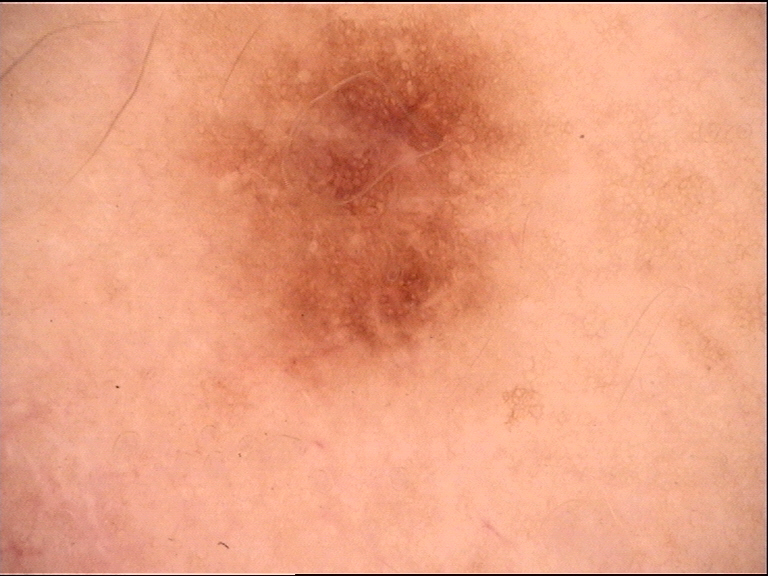Case:
- diagnostic label · dysplastic junctional nevus (expert consensus)